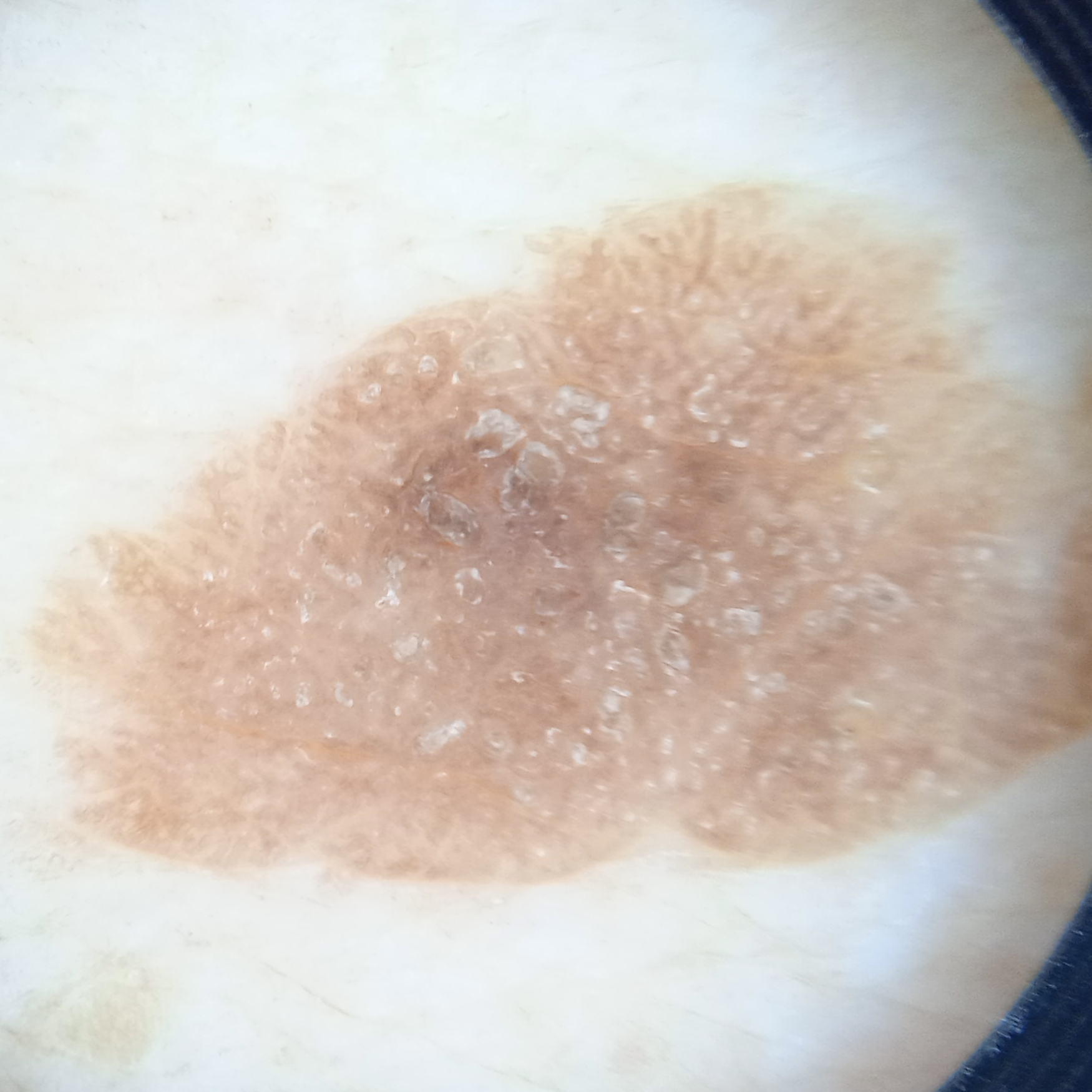Reviewed by four dermatologists, the consensus diagnosis was a seborrheic keratosis.